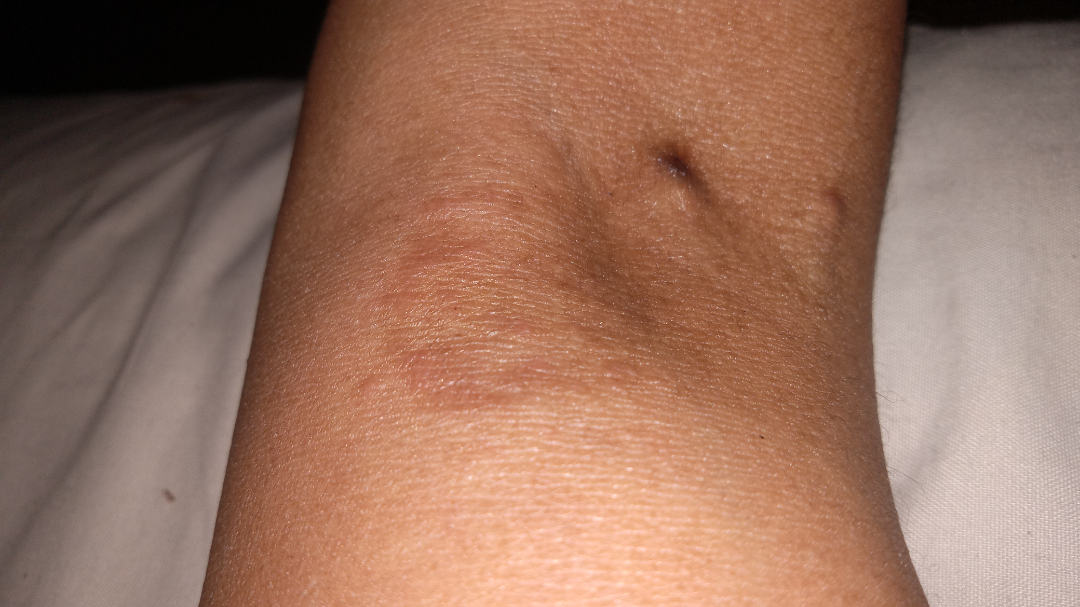Background:
Texture is reported as raised or bumpy. Female subject, age 50–59. The photo was captured at a distance.